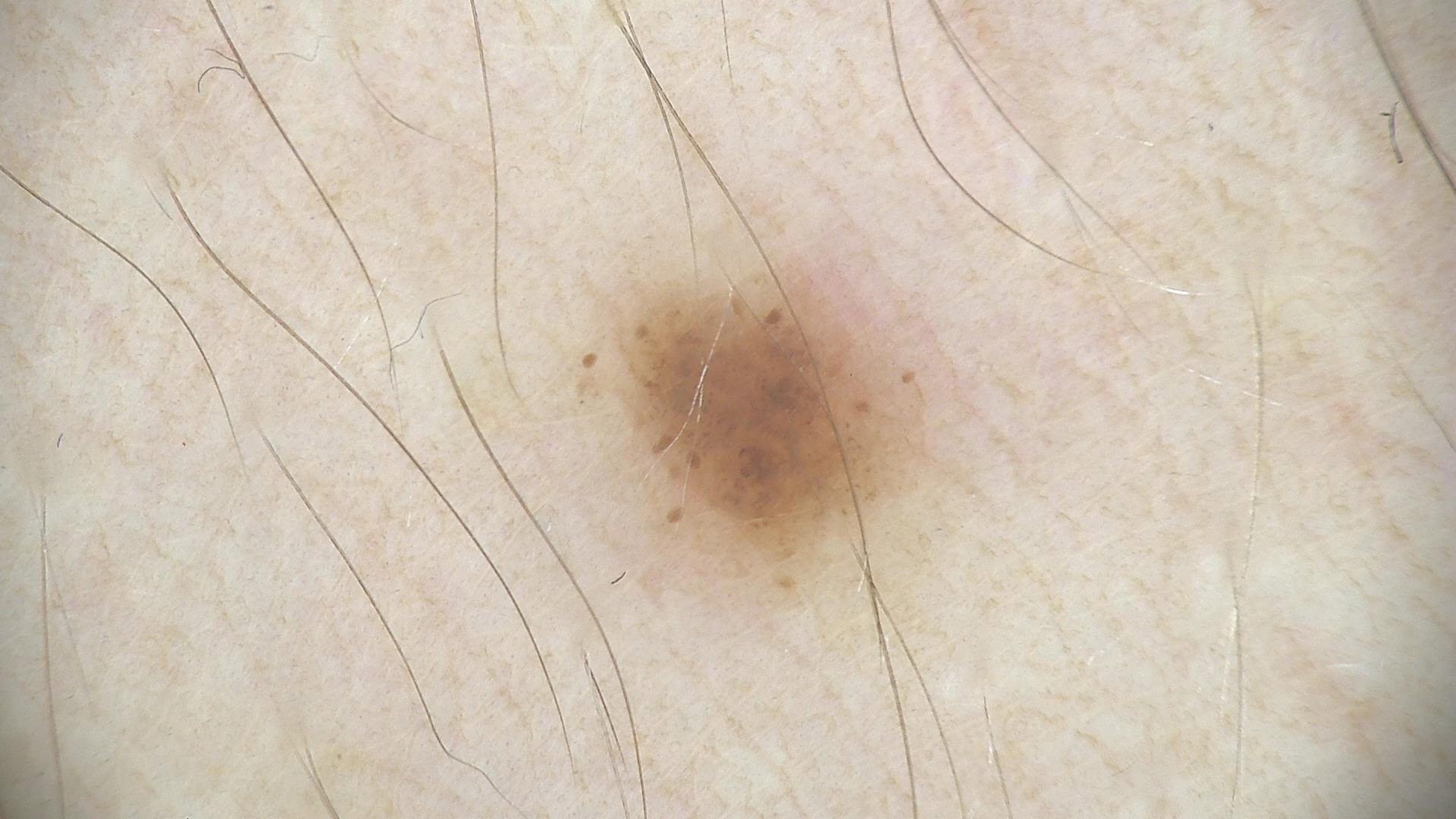Consistent with a dysplastic junctional nevus.